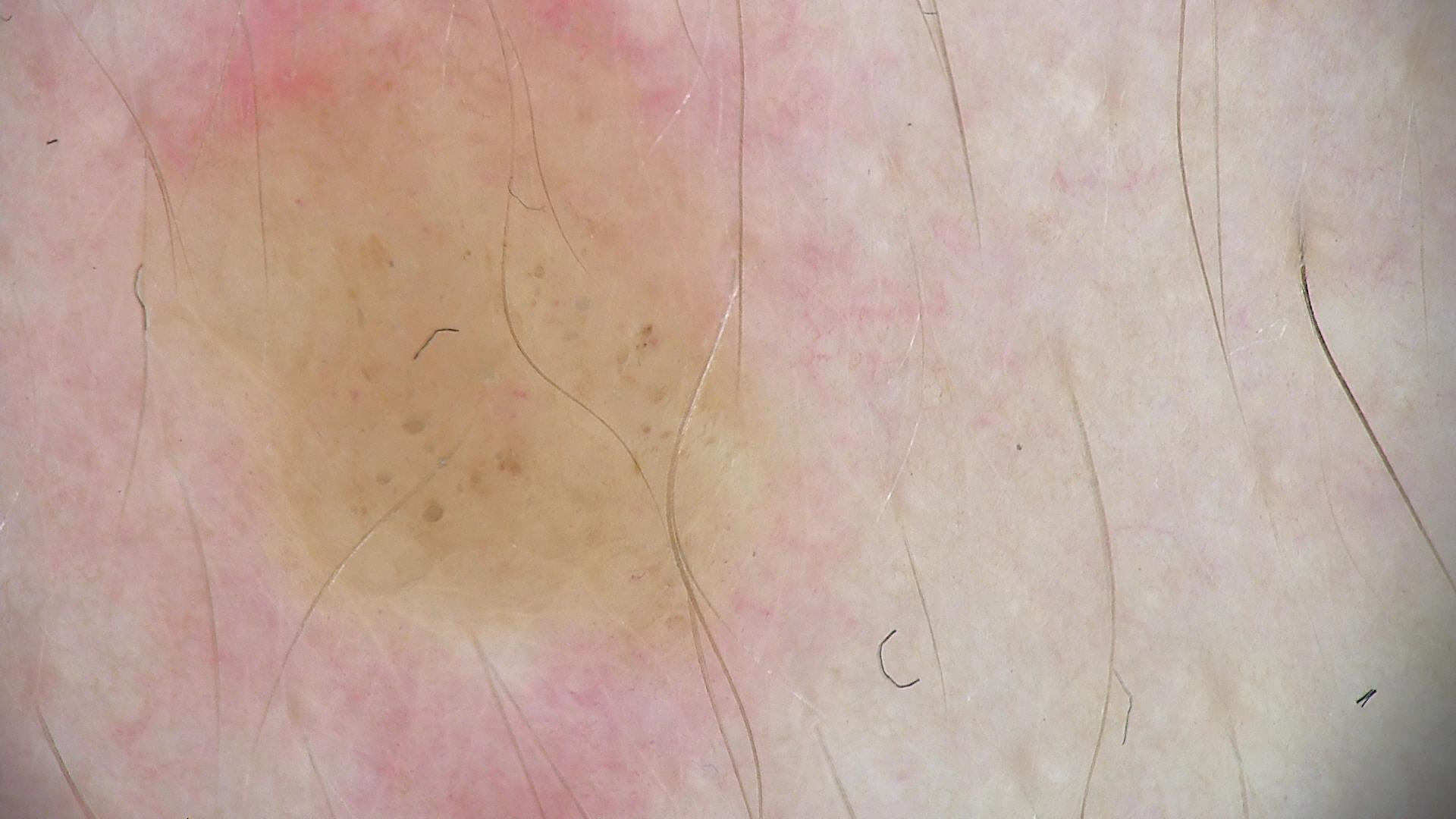A dermoscopic close-up of a skin lesion.
The diagnostic label was a dermal nevus.